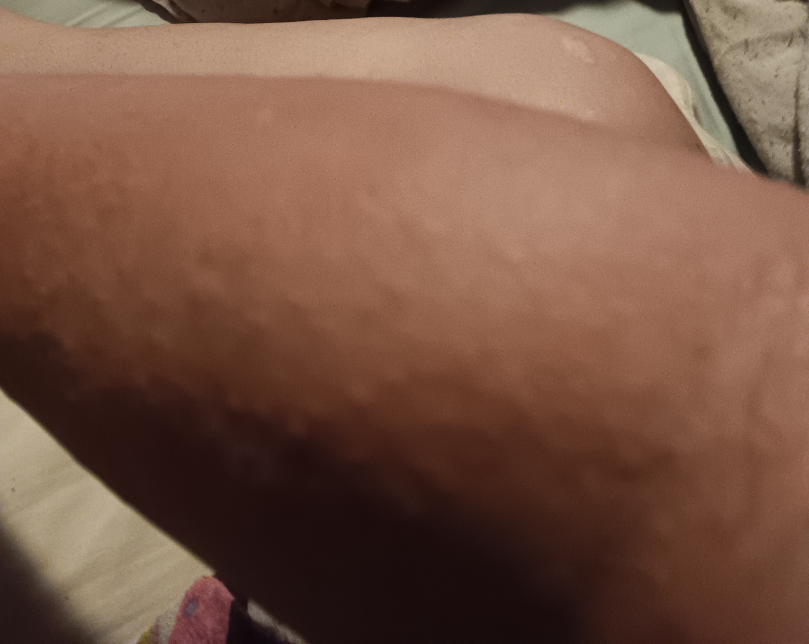Diagnostic features were not clearly distinguishable in this photograph. The photograph was taken at an angle. The patient reports the lesion is raised or bumpy. The affected area is the arm. Skin tone: FST IV. The patient reported no systemic symptoms. Reported duration is one to four weeks. Self-categorized by the patient as a rash. The lesion is associated with itching.